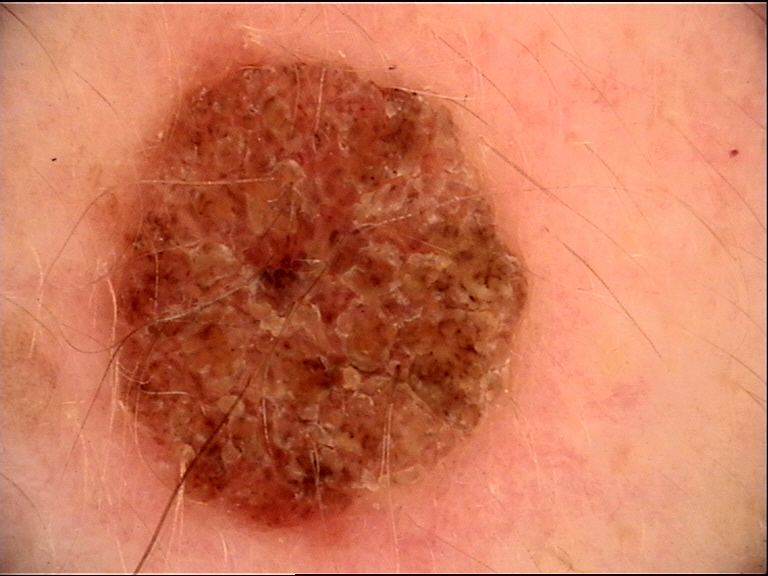modality — dermatoscopy
classification — banal
class — compound nevus (expert consensus)